A dermoscopic image of a skin lesion:
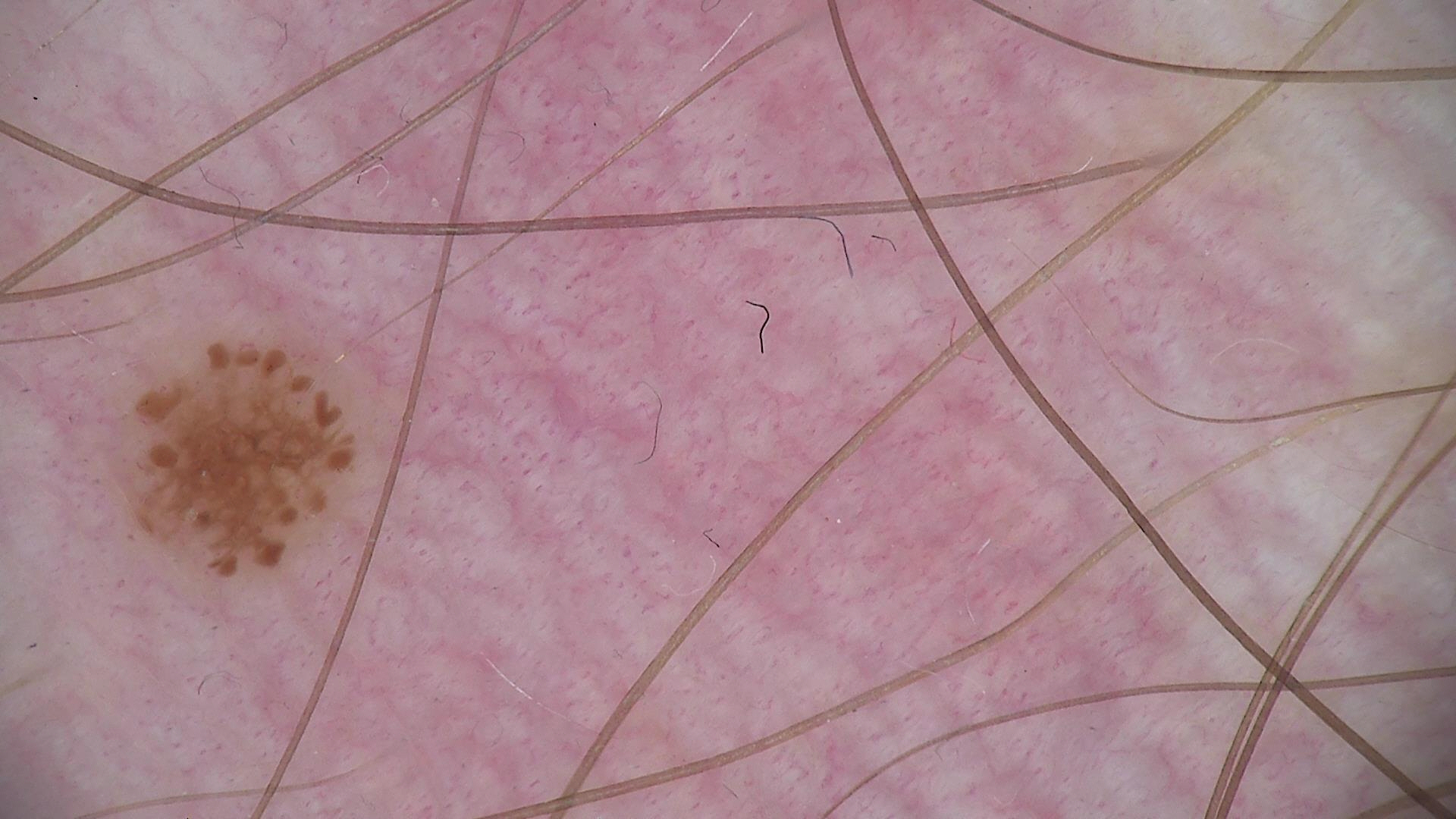Q: What is the diagnosis?
A: dysplastic junctional nevus (expert consensus)